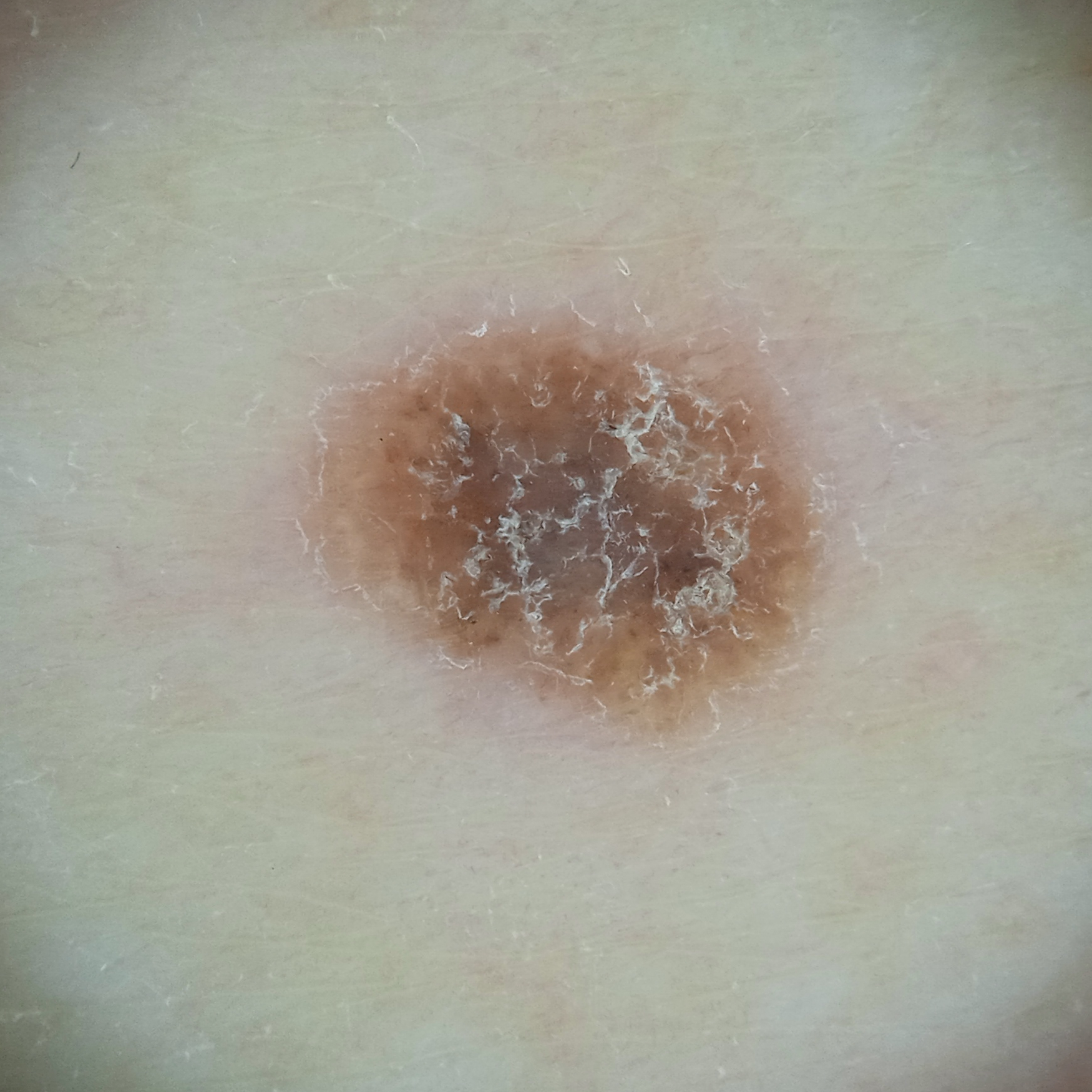Q: Tell me about the patient.
A: male, 79 years old
Q: What kind of image is this?
A: dermatoscopic image
Q: What was the diagnosis?
A: seborrheic keratosis (dermatologist consensus)